Dermoscopy of a skin lesion:
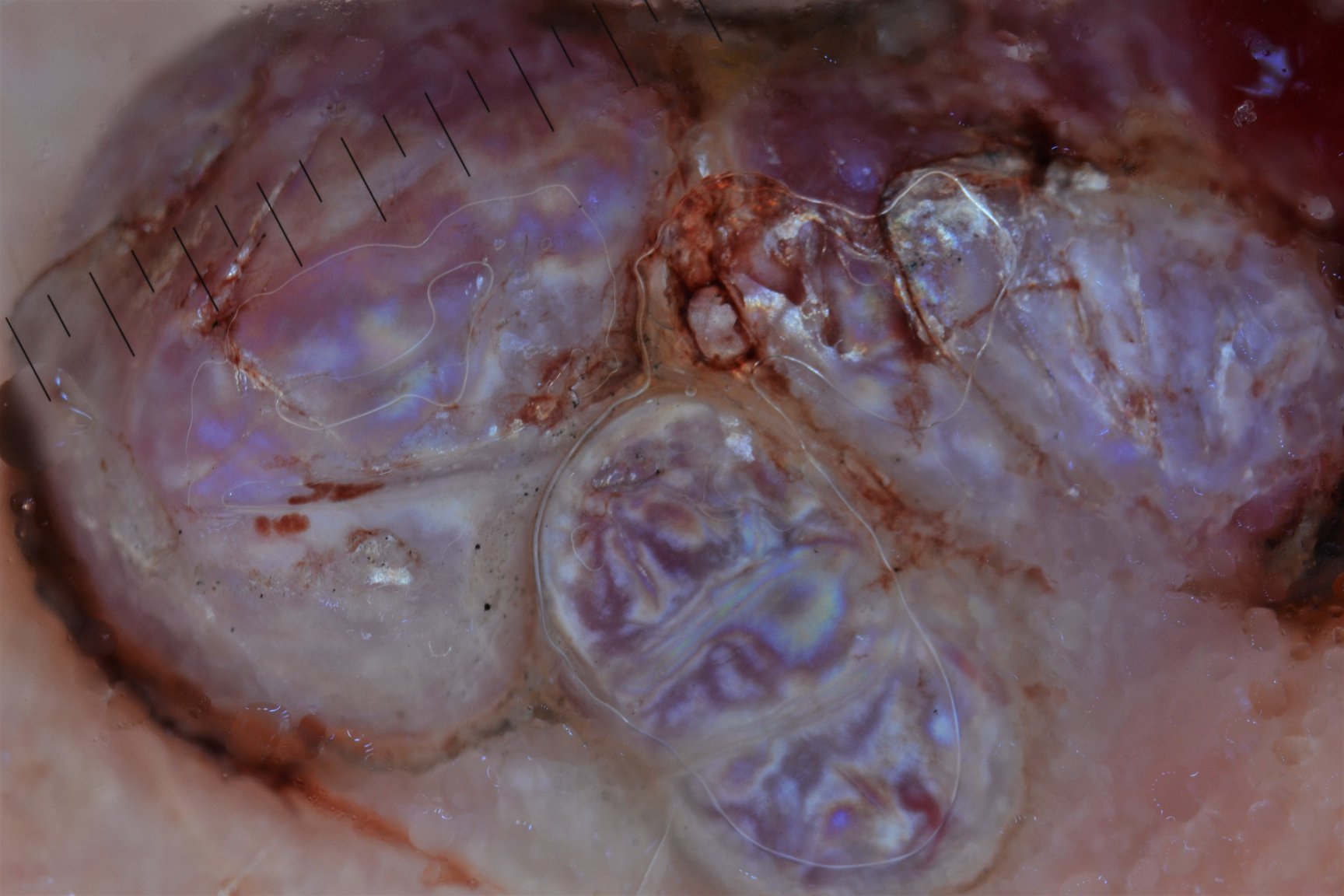• classification — vascular
• pathology — Kaposi sarcoma (biopsy-proven)